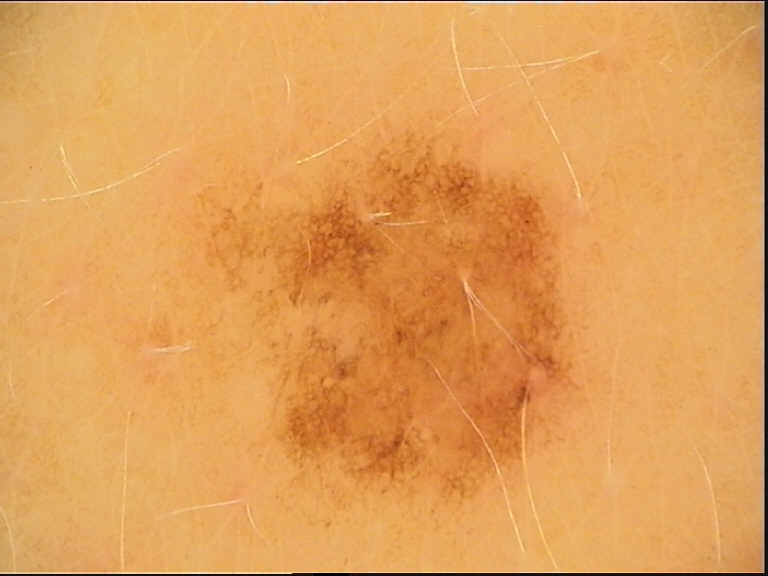Summary: A dermoscopic image of a skin lesion. Impression: Labeled as a dysplastic junctional nevus.